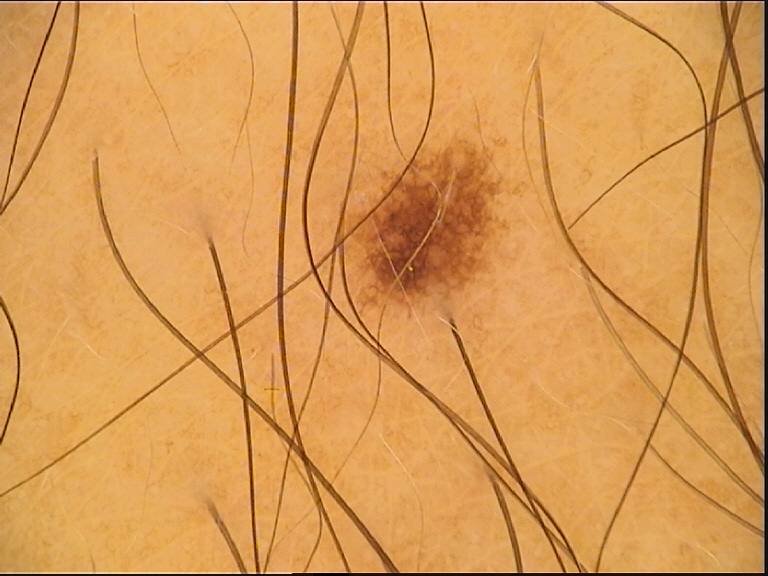Q: What kind of image is this?
A: dermatoscopy
Q: What was the diagnostic impression?
A: dysplastic junctional nevus (expert consensus)